Located on the arm; male subject, age 18–29; the patient did not report lesion symptoms; a close-up photograph; texture is reported as raised or bumpy and rough or flaky:
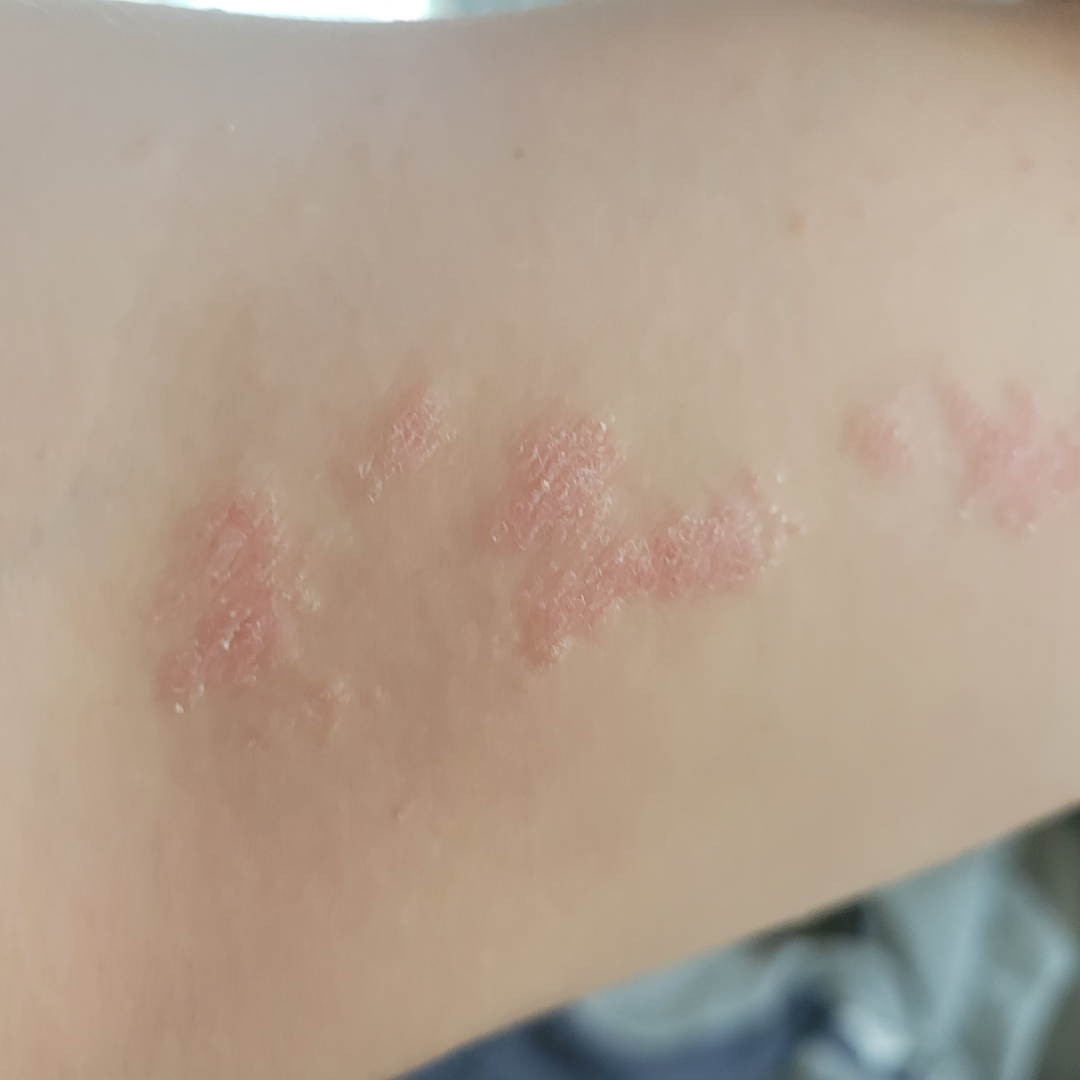assessment = indeterminate from the photograph.